A dermatoscopic image of a skin lesion — 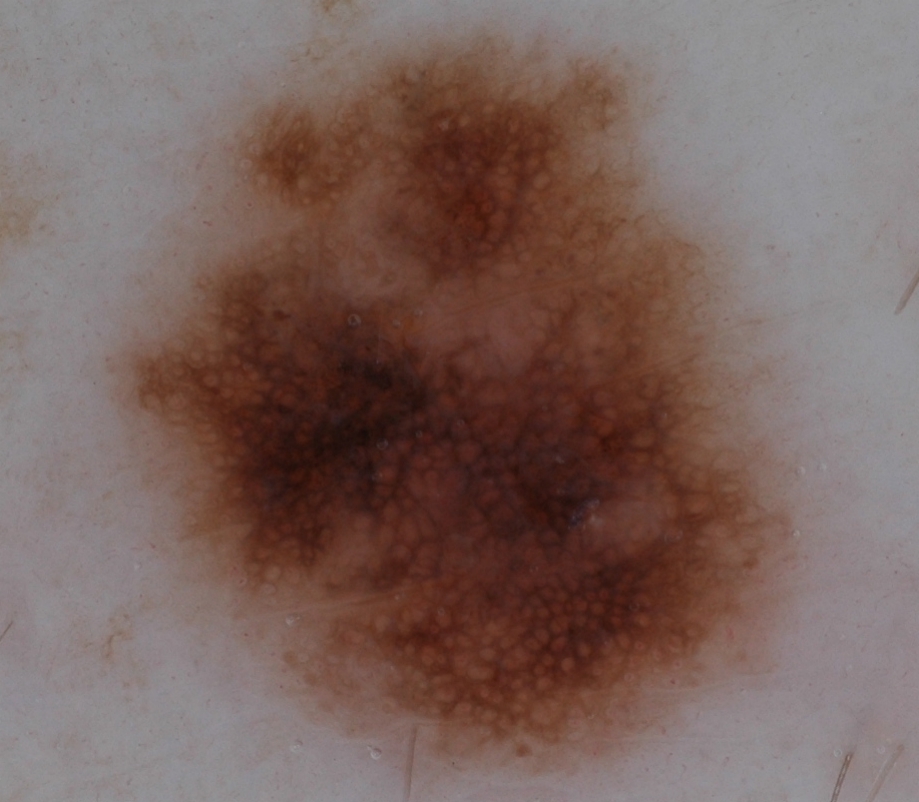{
  "lesion_location": {
    "bbox_xyxy": [
      102,
      25,
      799,
      774
    ]
  },
  "lesion_extent": {
    "approx_field_fraction_pct": 51
  },
  "dermoscopic_features": {
    "present": [
      "pigment network"
    ],
    "absent": [
      "negative network",
      "milia-like cysts",
      "globules",
      "streaks"
    ]
  },
  "diagnosis": {
    "name": "melanocytic nevus",
    "malignancy": "benign",
    "lineage": "melanocytic",
    "provenance": "clinical"
  }
}